A dermoscopic image of a skin lesion.
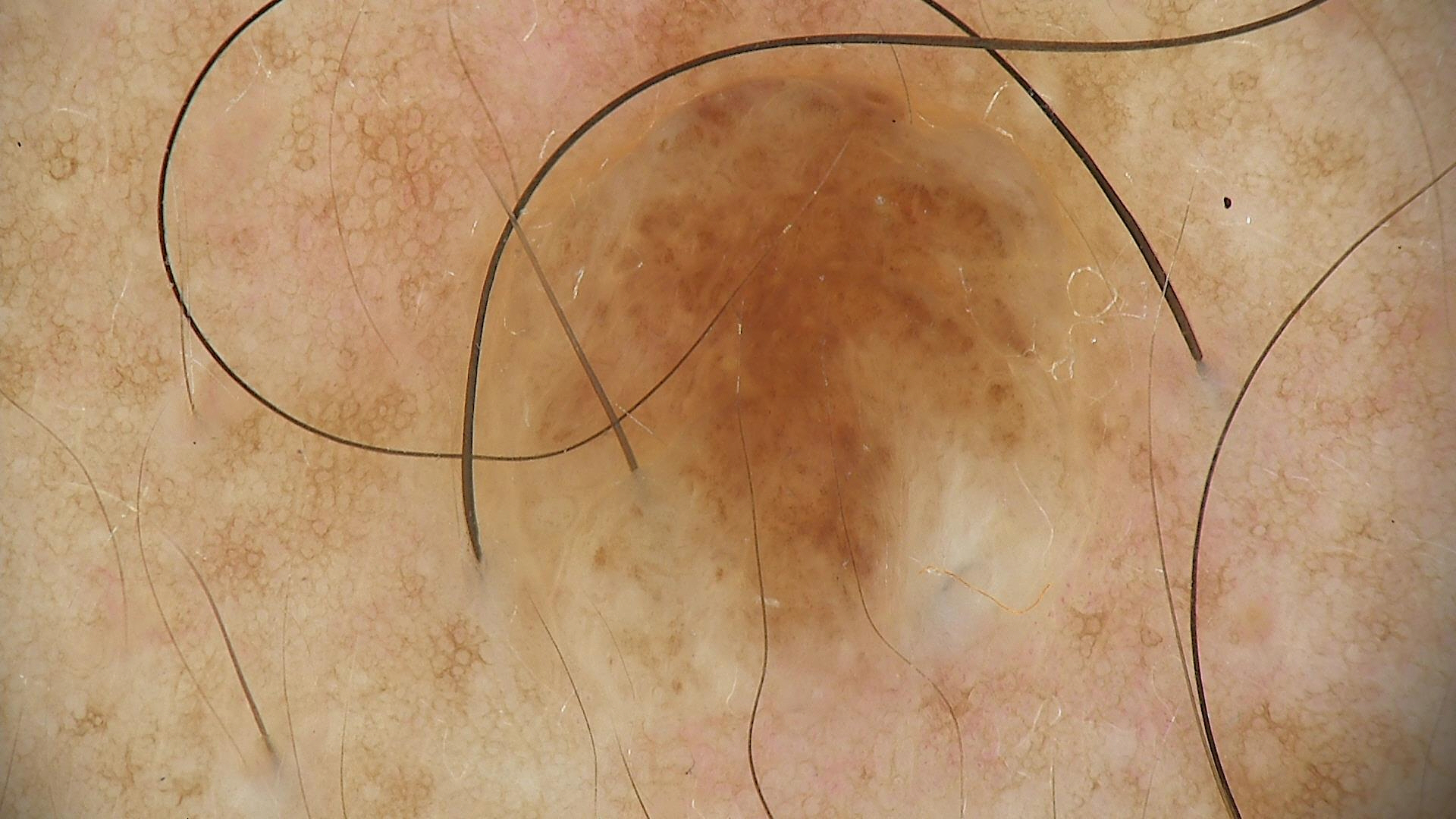Labeled as a banal lesion — a dermal nevus.